An image taken at an angle:
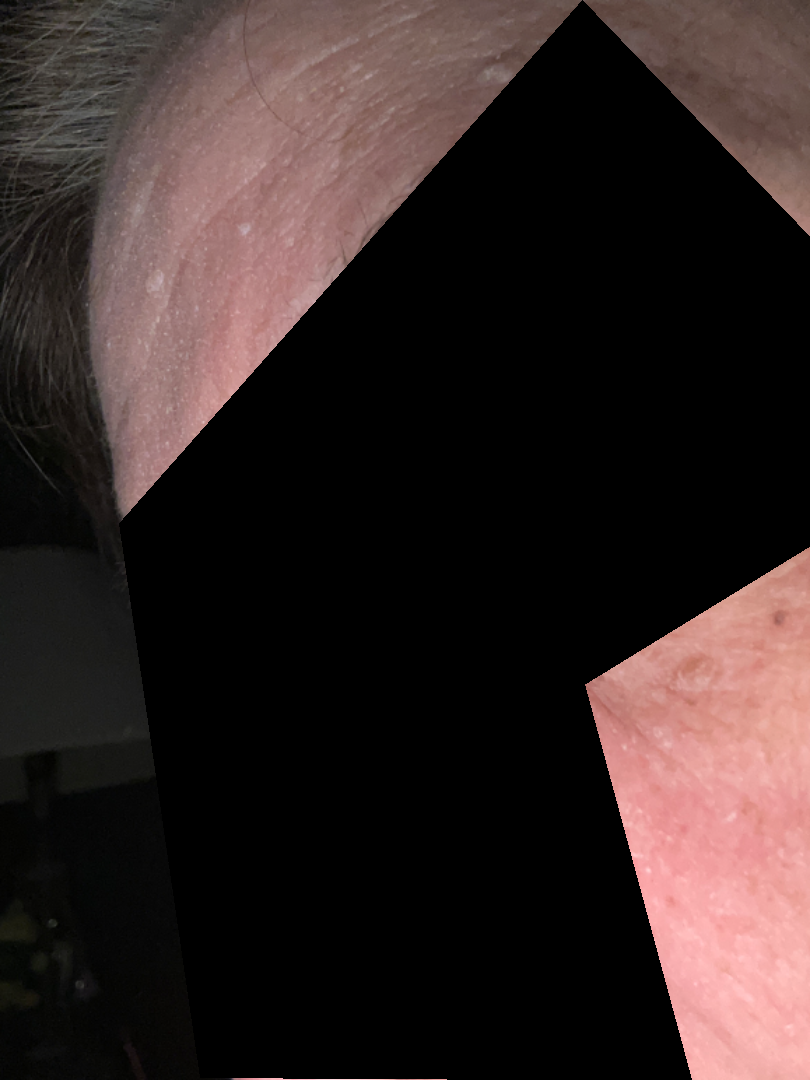Background: Skin tone: Fitzpatrick phototype I. Findings: On photographic review, consistent with Seborrheic Dermatitis.